A dermatoscopic image of a skin lesion:
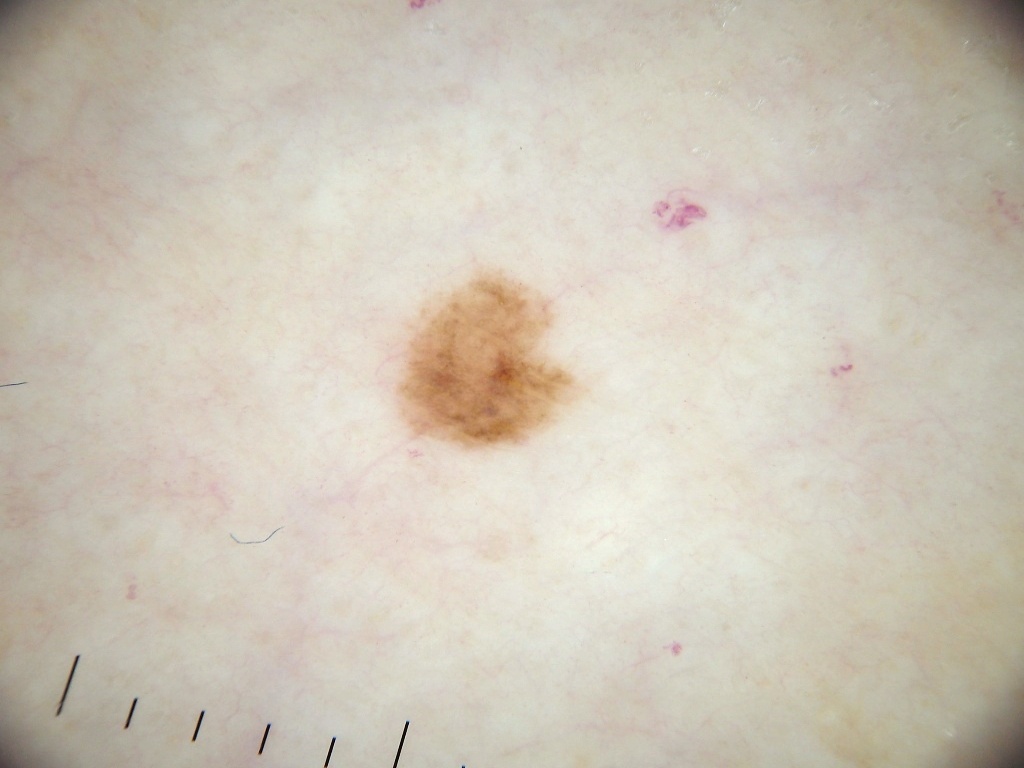The lesion occupies roughly 3% of the field.
The dermoscopic pattern shows neither globules nor streaks.
As (left, top, right, bottom), lesion location: <box>393, 266, 580, 450</box>.
The lesion was assessed as a benign lesion.